On a questionnaire the patient reported a personal history of skin cancer; collected as part of a research study, without a referral diagnosis; the patient describes having a moderate number of moles; dermoscopy of a skin lesion.
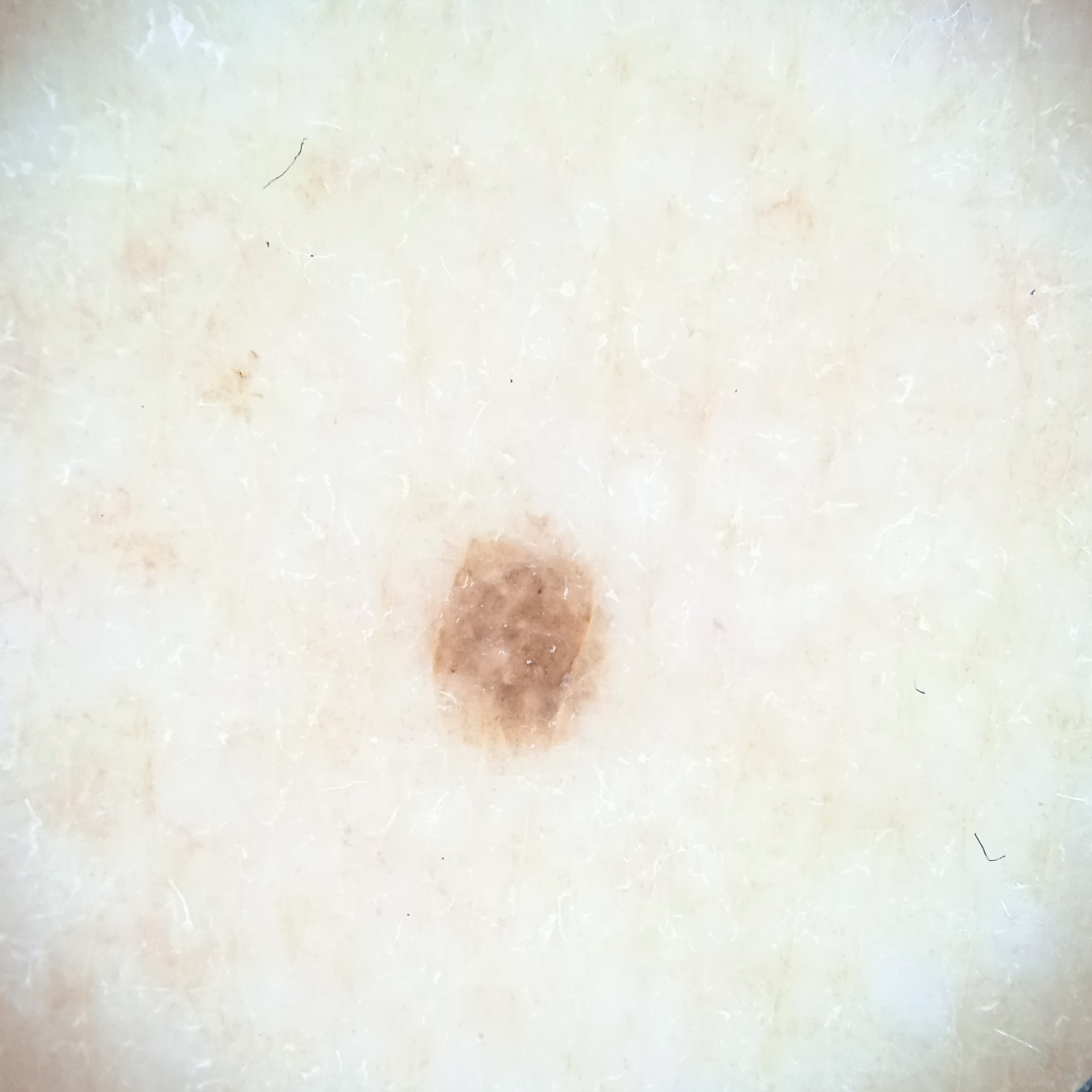| feature | finding |
|---|---|
| site | an arm |
| diameter | 2.5 mm |
| assessment | melanocytic nevus (dermatologist consensus) |